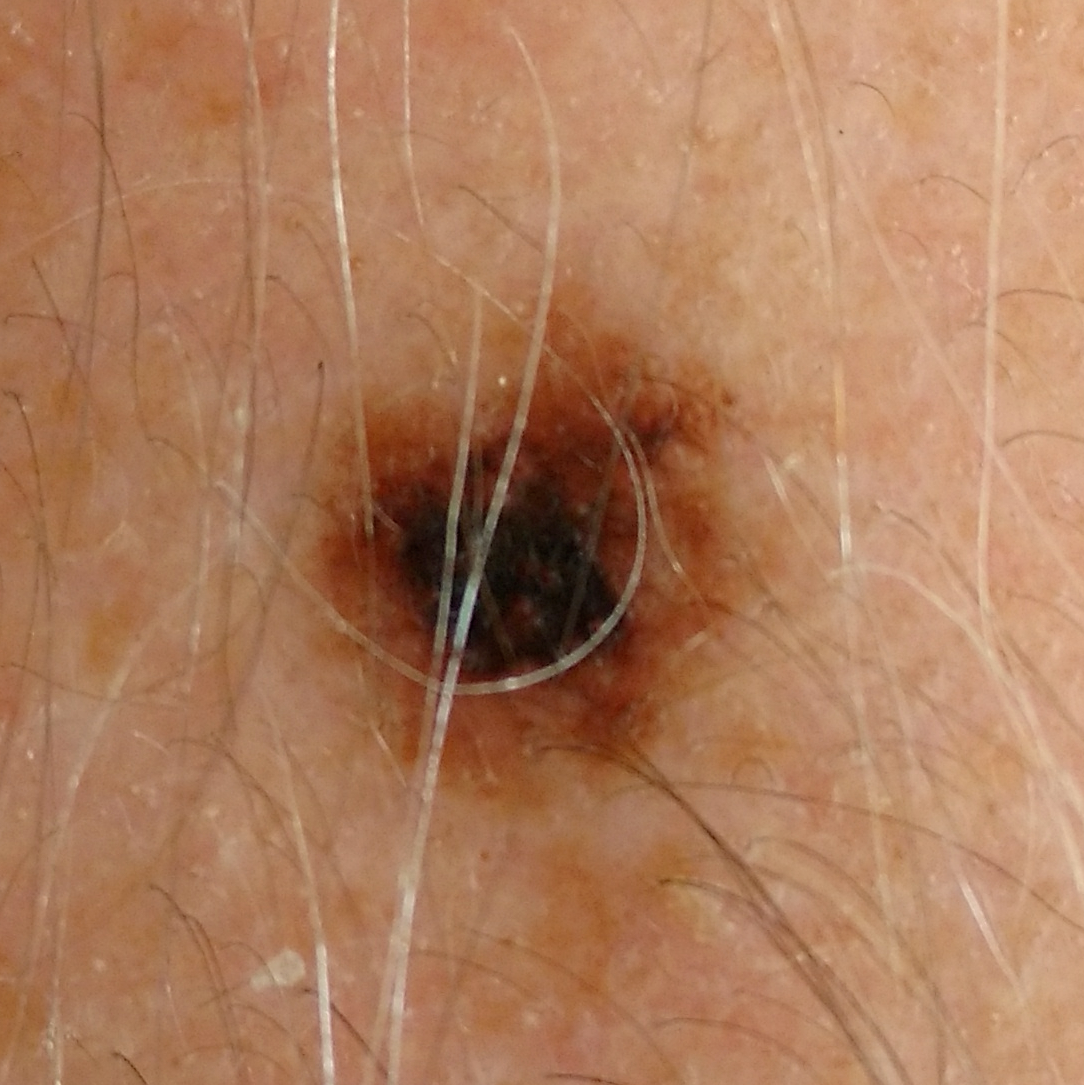Confirmed on histopathology as a melanoma.